A dermoscopic close-up of a skin lesion, the patient is a female approximately 45 years of age — 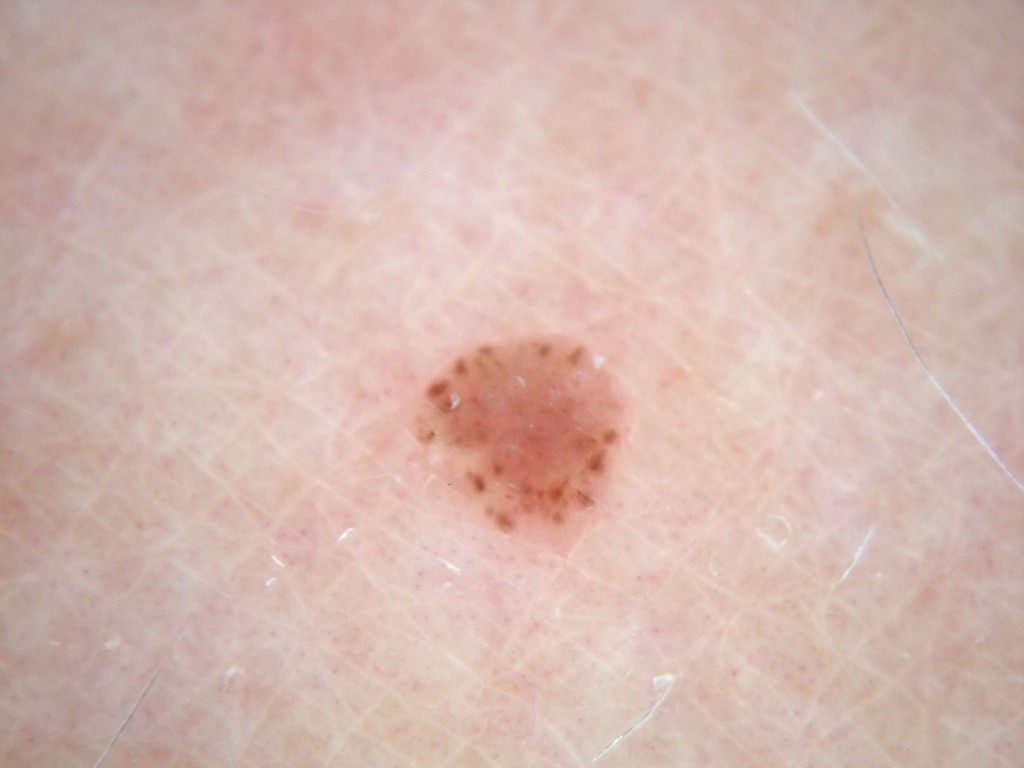absent dermoscopic findings = pigment network, milia-like cysts, negative network, globules, and streaks
location = <bbox>405, 332, 626, 548</bbox>
assessment = a melanocytic nevus